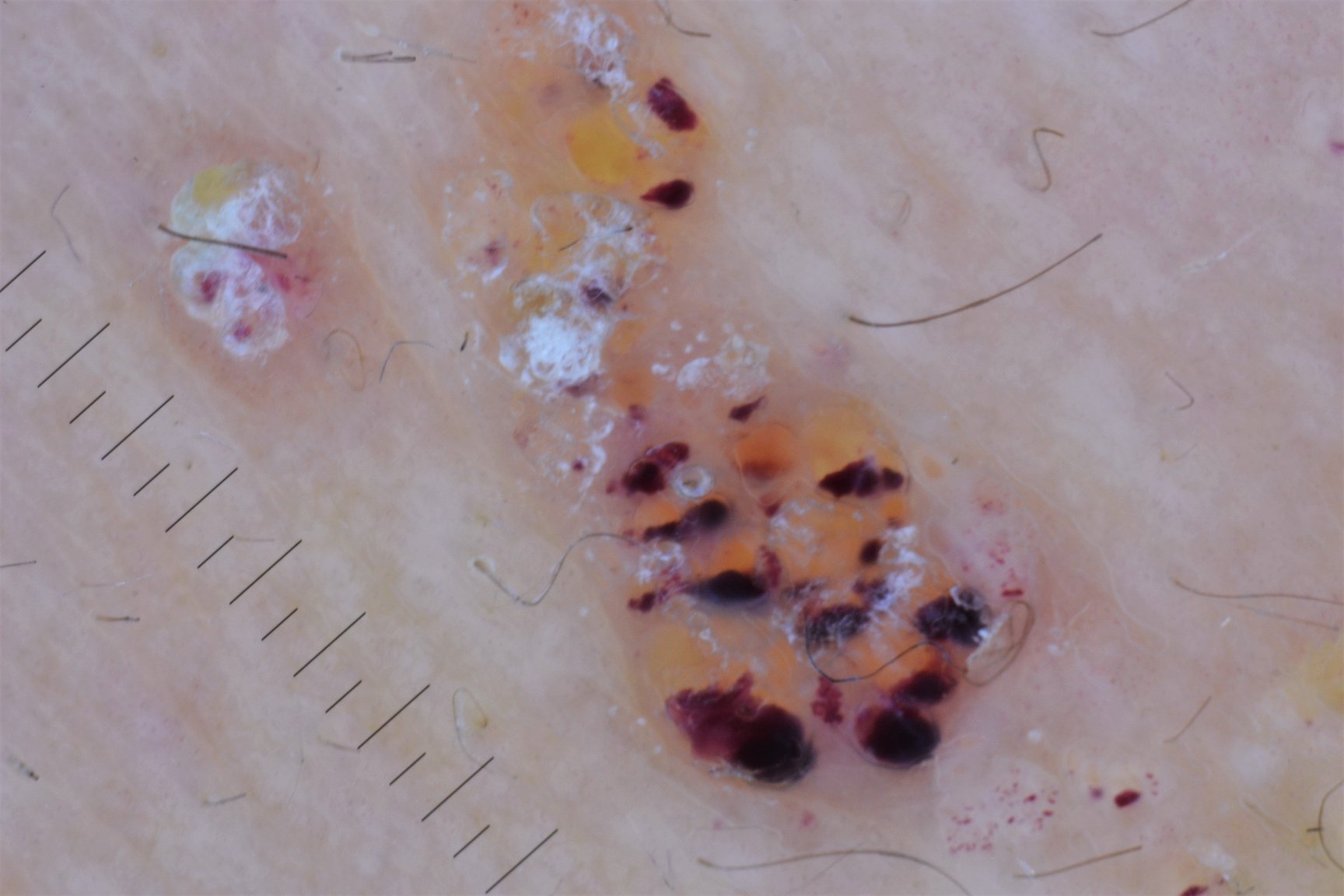Q: What is this lesion?
A: lymphangioma (expert consensus)